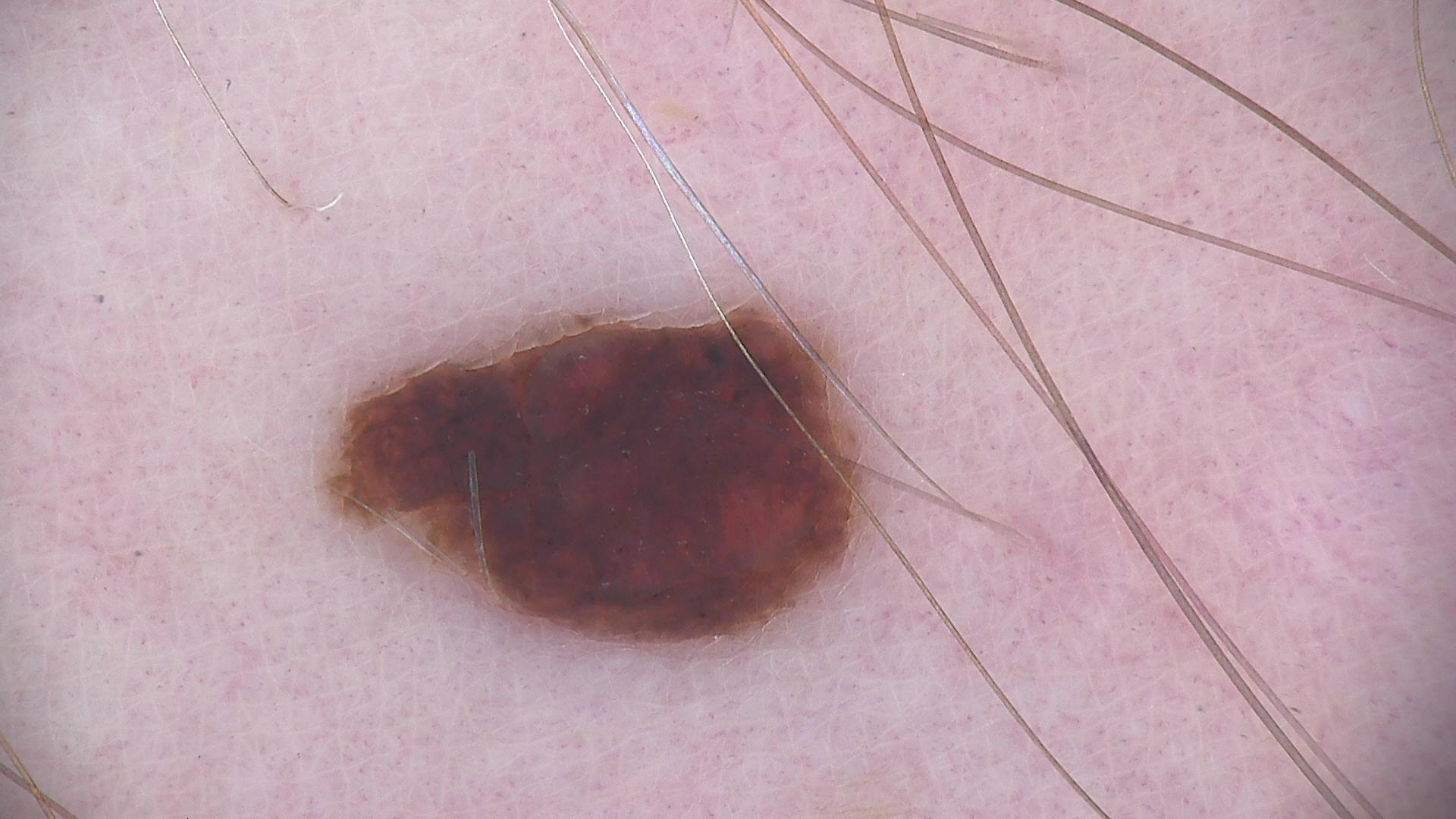A dermoscopic close-up of a skin lesion. Classified as a banal lesion — a compound nevus.